A female subject in their 60s · a clinical photograph of a skin lesion: 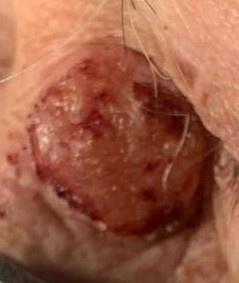Case summary: The lesion involves the head or neck. Conclusion: Histopathologically confirmed as a squamous cell carcinoma.